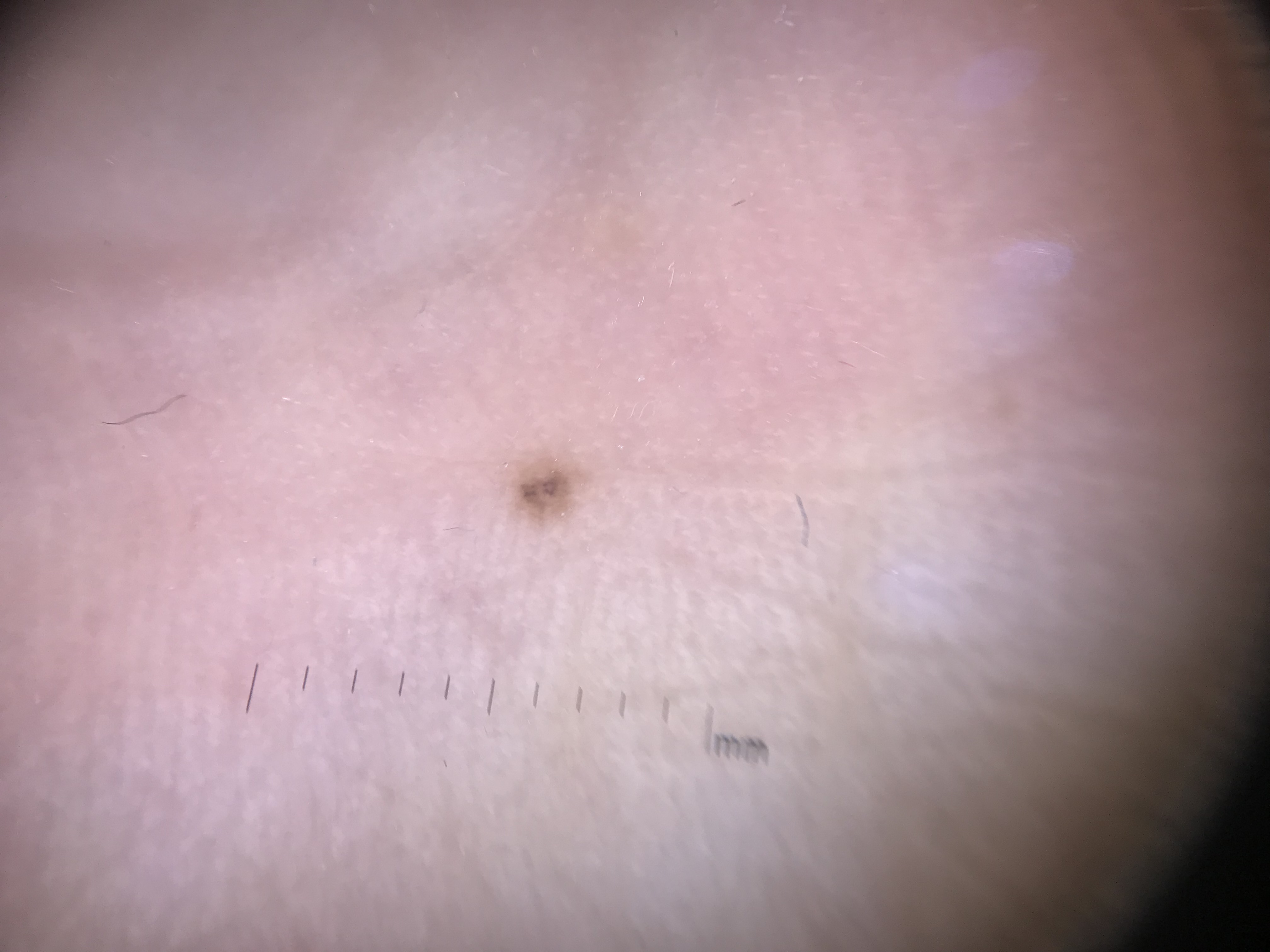Case:
A skin lesion imaged with a dermatoscope.
Impression:
Diagnosed as a banal lesion — an acral junctional nevus.